The patient was assessed as FST III; contact-polarized dermoscopy of a skin lesion; a female patient roughly 45 years of age — 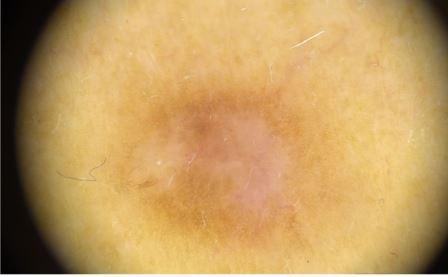Image and clinical context: Located on a lower extremity. Impression: The clinical assessment was a lesion of fibro-histiocytic origin — a dermatofibroma.